A dermoscopic photograph of a skin lesion.
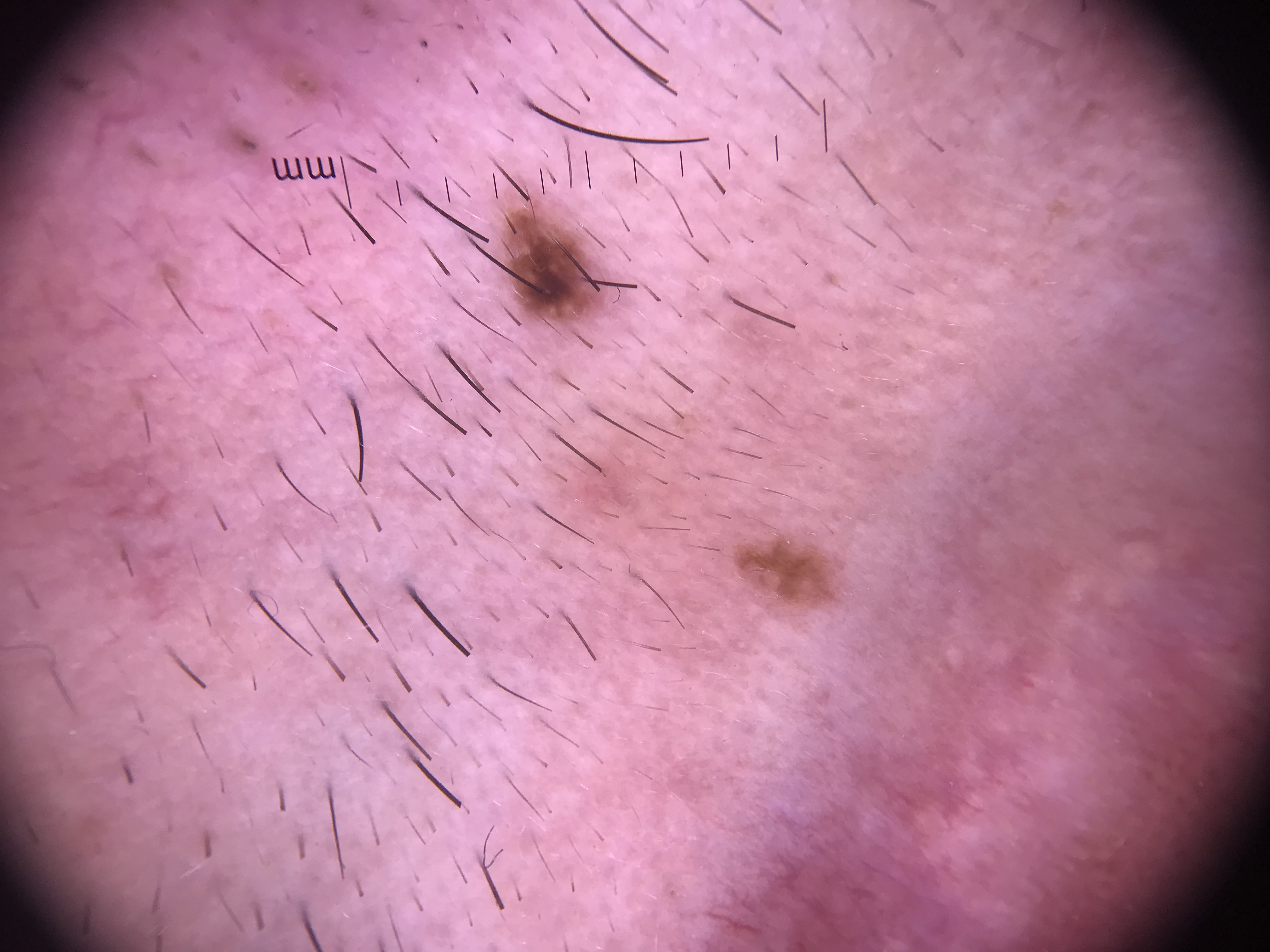Case:
– classification · banal, compound
– label · Miescher nevus (expert consensus)